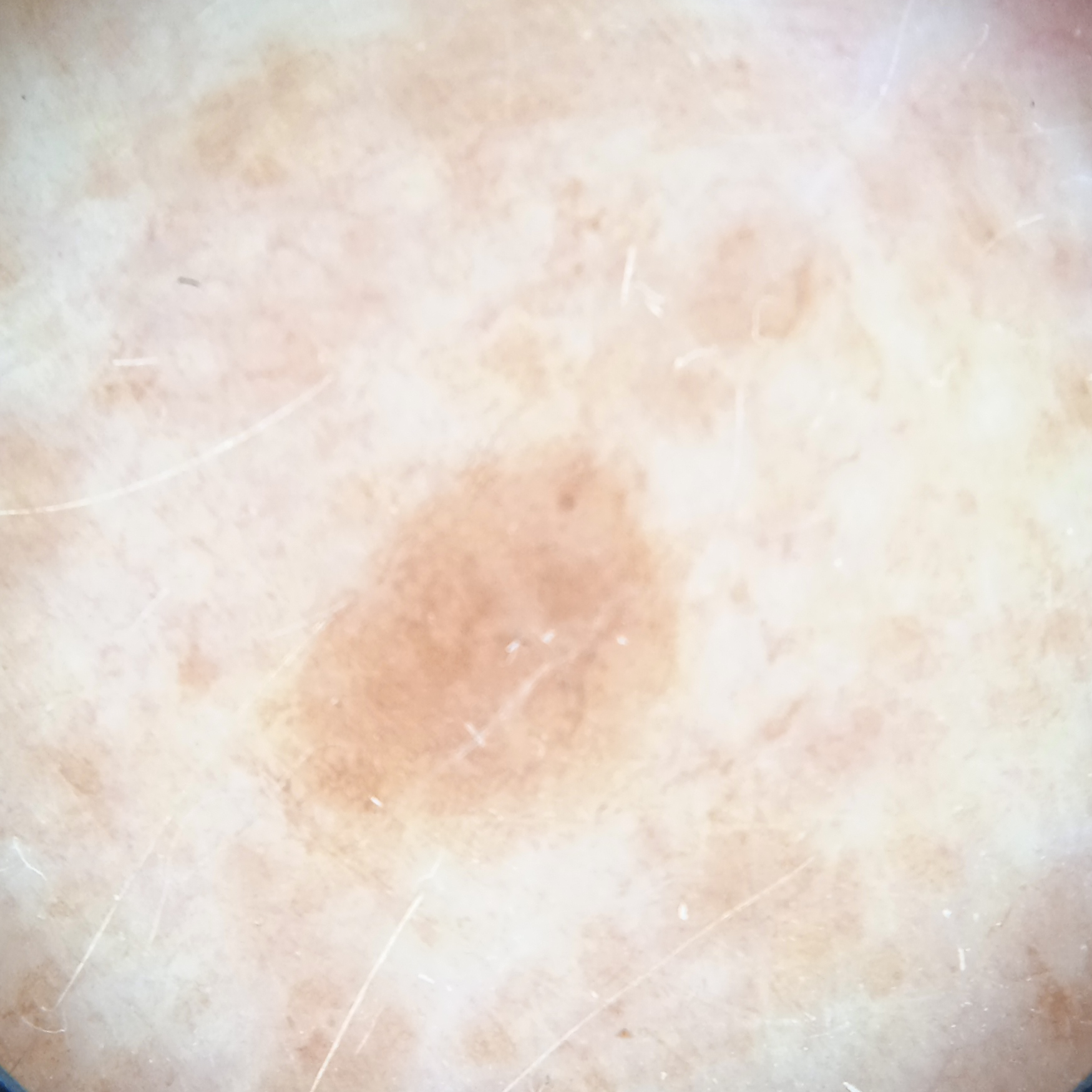  diagnosis:
    name: seborrheic keratosis
    malignancy: benign